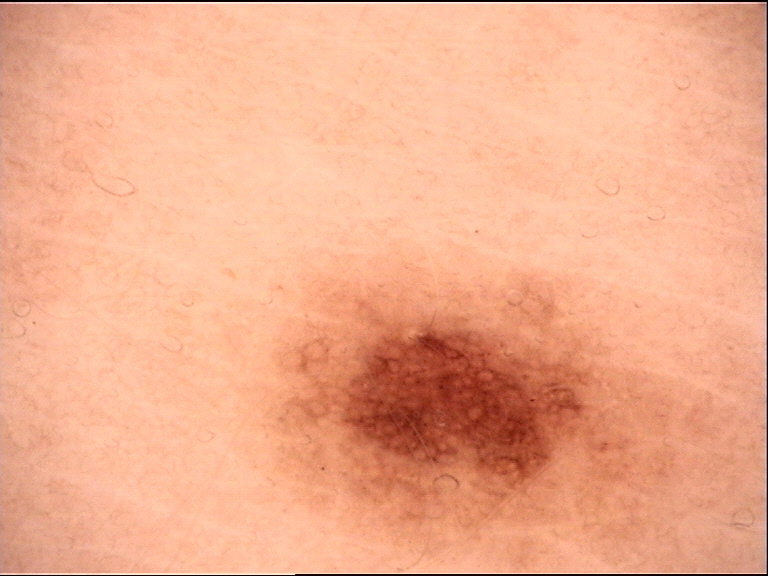Diagnosed as a dysplastic junctional nevus.